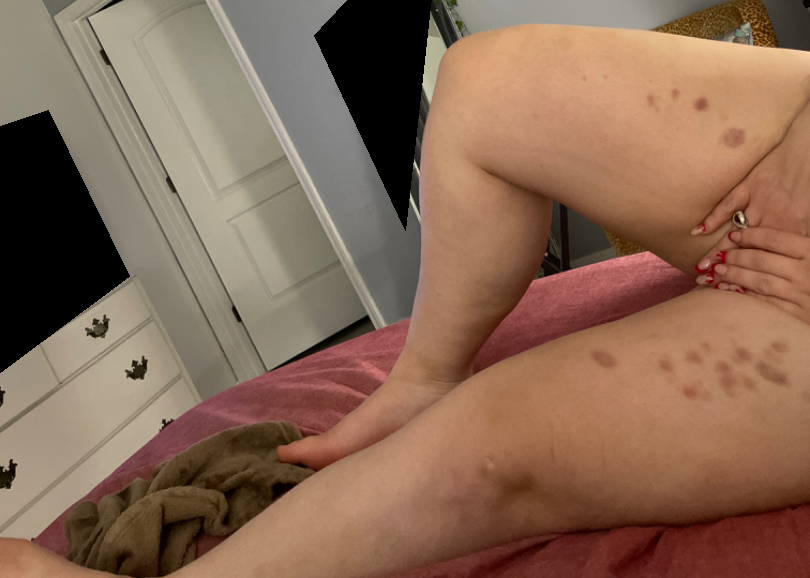Notes:
* image framing — at a distance
* patient — female, age 18–29
* body site — leg
* diagnostic considerations — the impression on review was ecchymoses